A dermoscopy image of a single skin lesion: 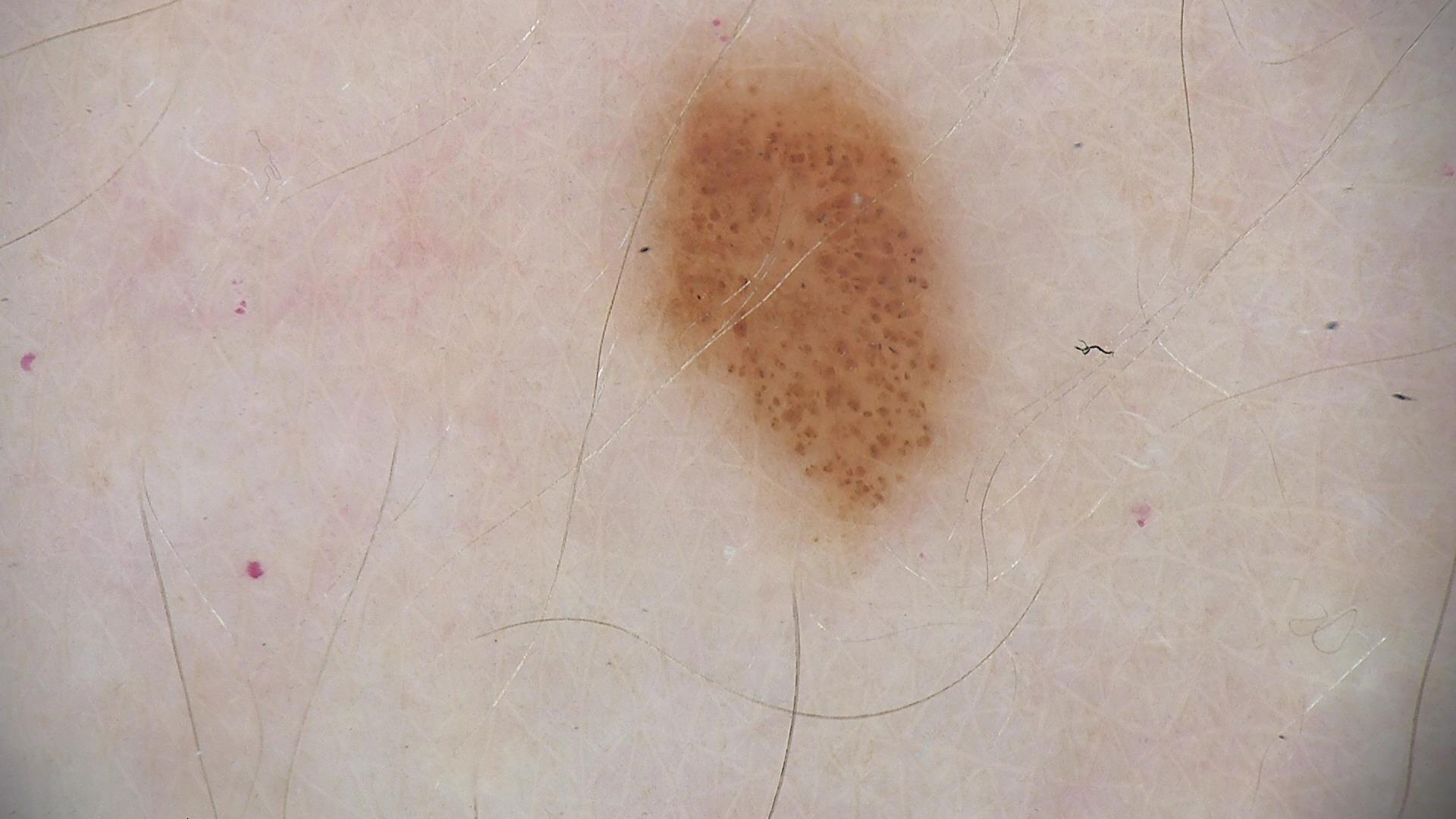Conclusion: Consistent with a benign lesion — a dysplastic junctional nevus.